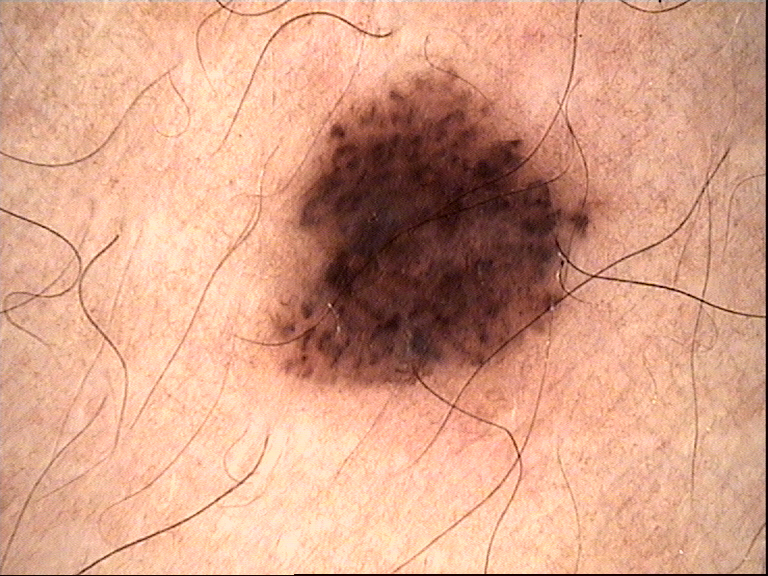class — dysplastic compound nevus (expert consensus).